The patient describes having a moderate number of moles; on a questionnaire the patient reported a family history of skin cancer and a personal history of cancer; the patient says their skin tans without first burning; a female patient 64 years of age; referred with a clinical suspicion of melanocytic nevus:
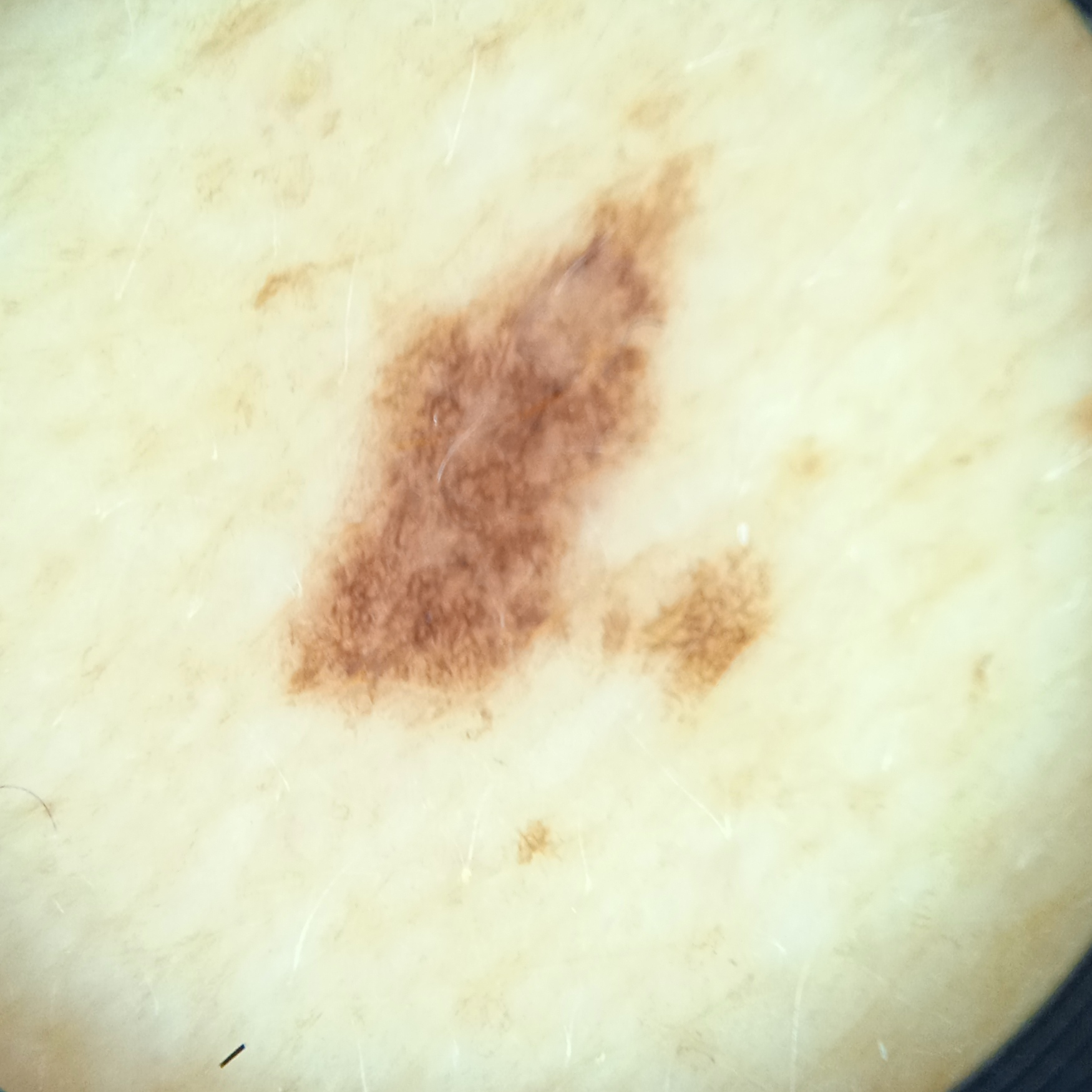| field | value |
|---|---|
| body site | the back |
| diagnostic label | atypical (dysplastic) nevus — biopsy-proven |